Symptoms reported: itching, burning and pain. Self-categorized by the patient as a rash. Close-up view — 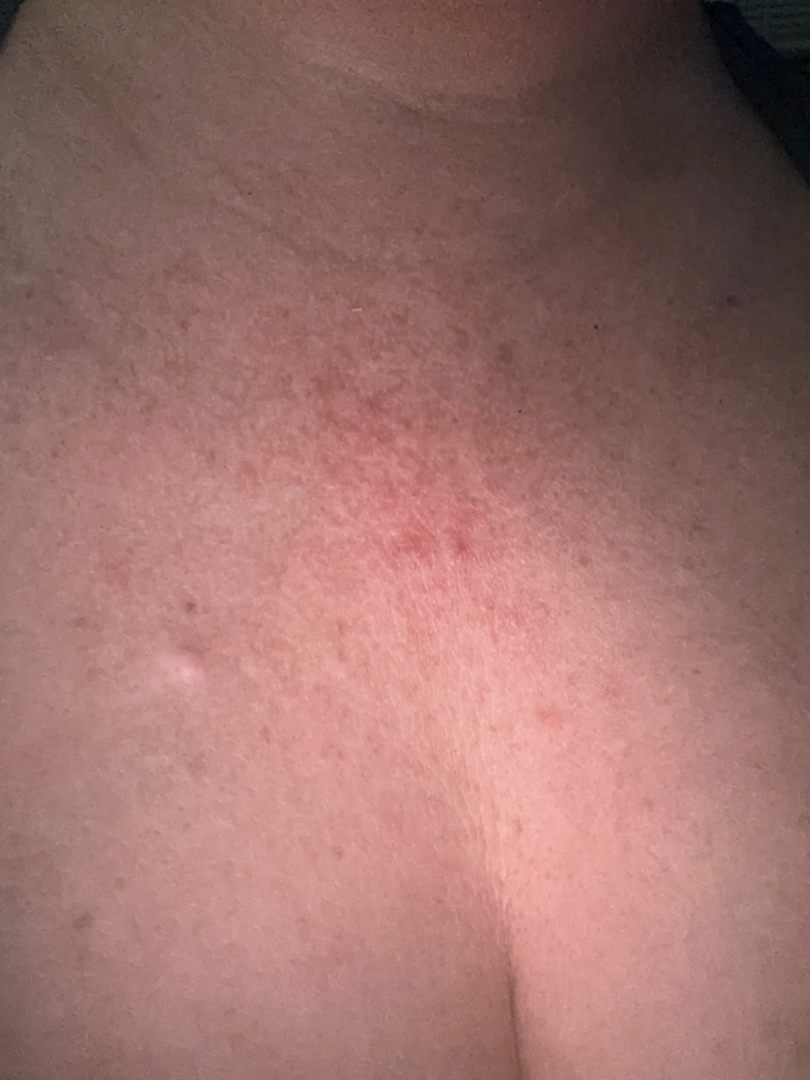The condition could not be reliably identified from the image.